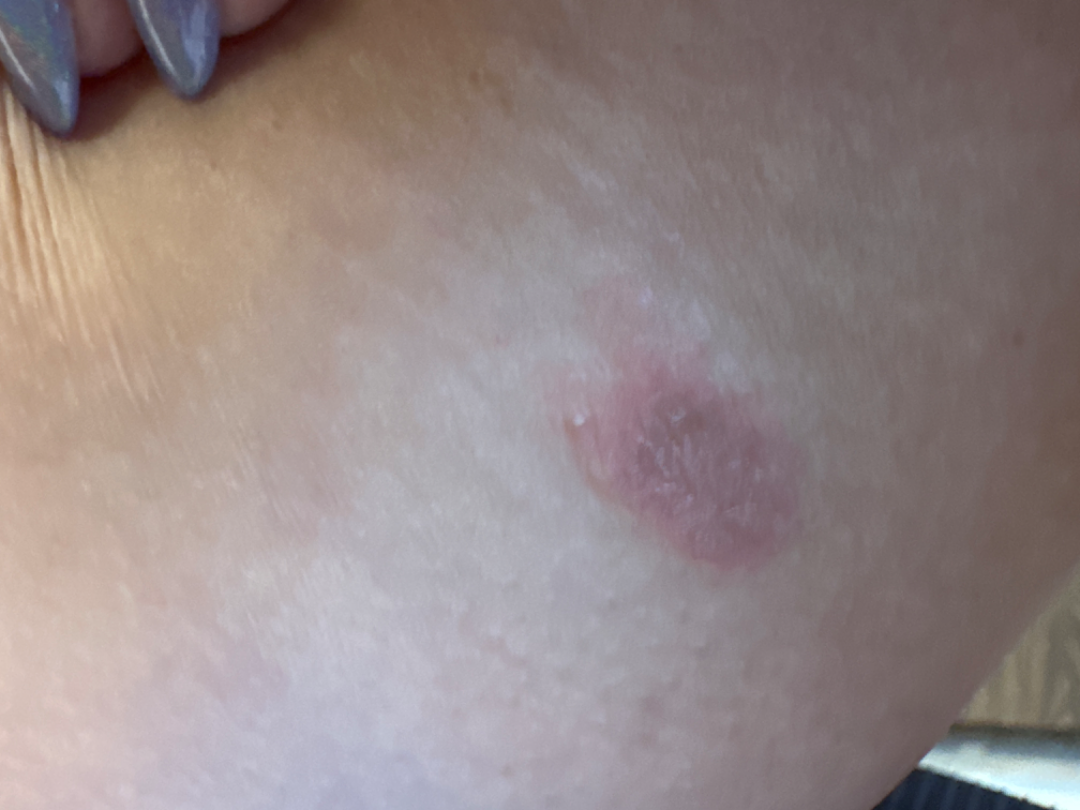{"assessment": "ungradable on photographic review", "shot_type": "close-up", "skin_tone": {"fitzpatrick": "III"}}